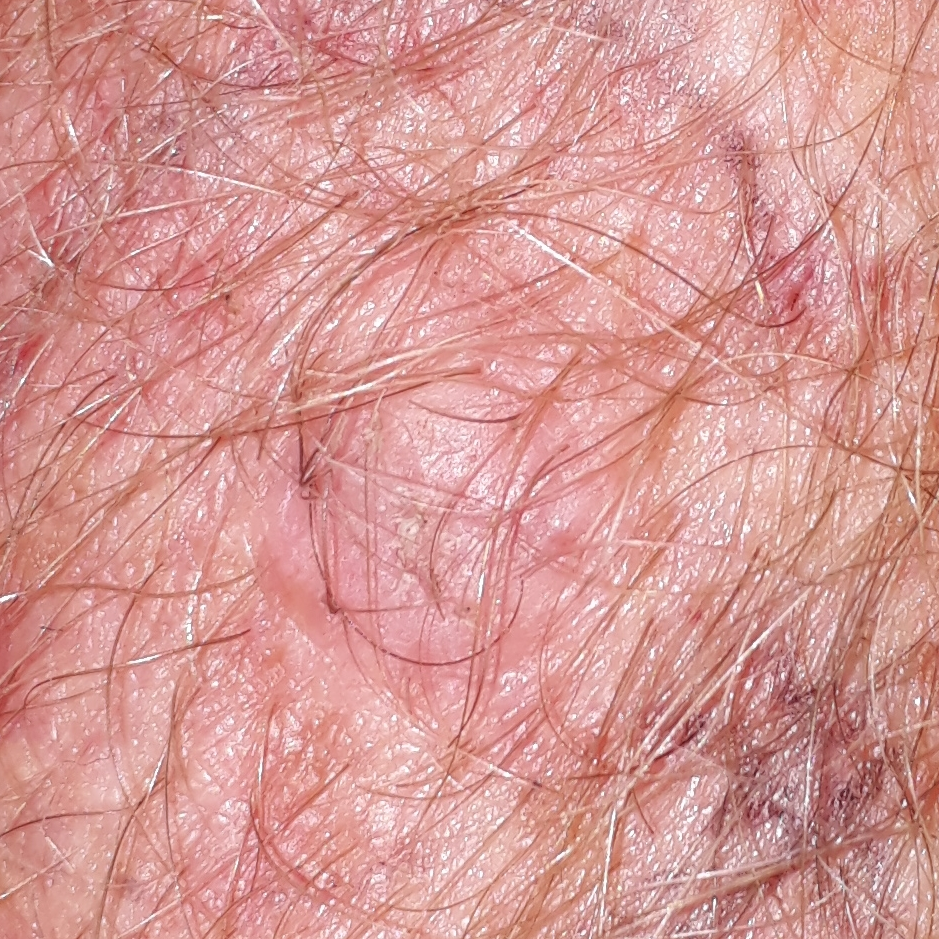Patient and lesion:
The chart notes pesticide exposure, prior malignancy (patient or family), and prior skin cancer (patient or family). A male subject age 45. The lesion is on a forearm. The lesion measures approximately 10 × 10 mm.
Pathology:
Biopsy-confirmed as a lesion of indeterminate malignant potential — an actinic keratosis.